The photo was captured at an angle. Located on the head or neck. The contributor is a male aged 40–49:
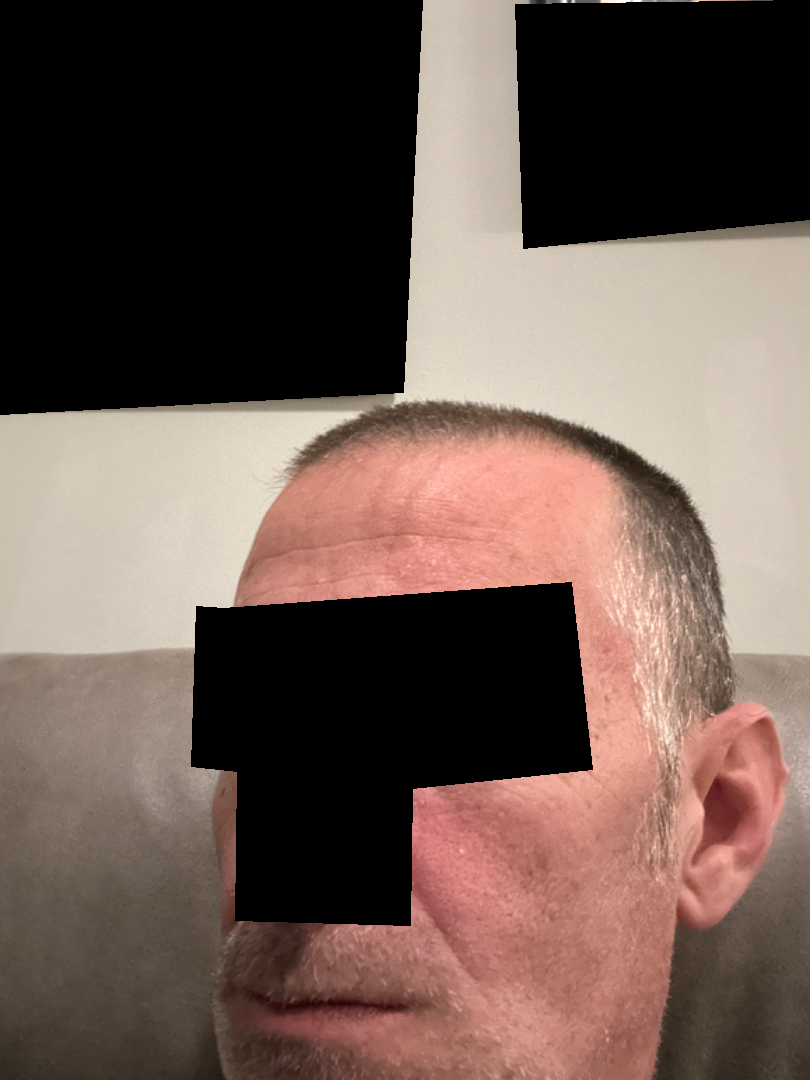No discernible pathology was noted by the reviewing dermatologist.